A subject 53 years old; a clinical photo of a skin lesion taken with a smartphone:
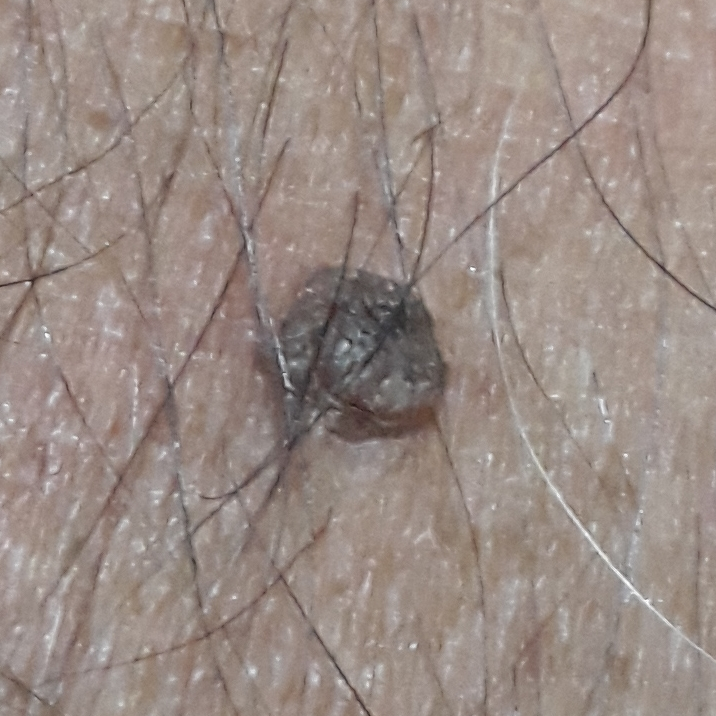region=a forearm
patient-reported symptoms=elevation, itching
diagnosis=seborrheic keratosis (clinical consensus)